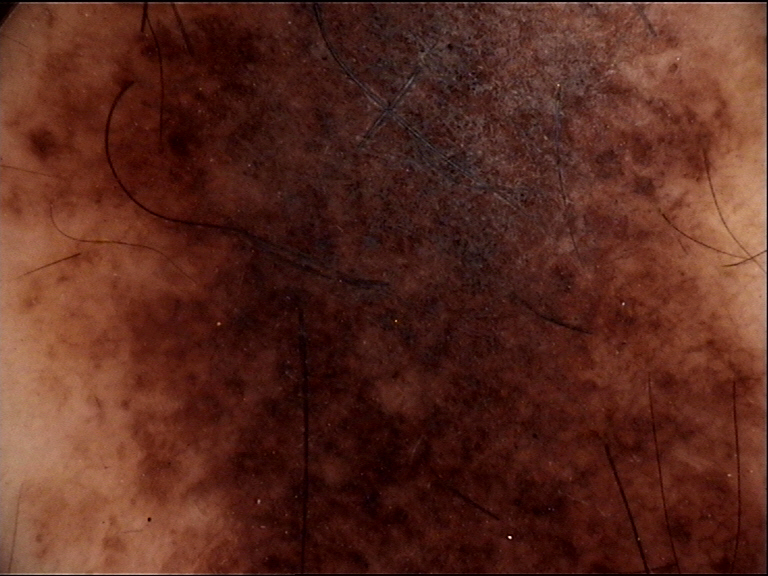image type: dermoscopy | category: banal | diagnostic label: congenital compound nevus (expert consensus).